The arm is involved, the photo was captured at an angle — 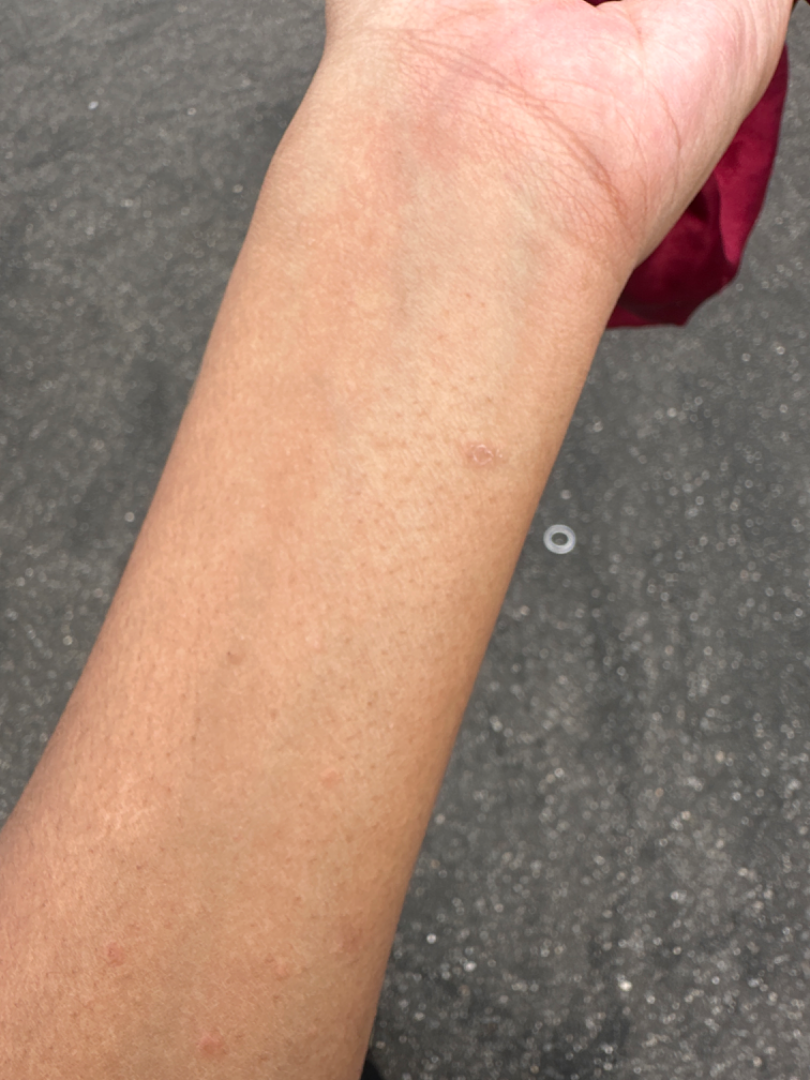{
  "systemic_symptoms": "none reported",
  "duration": "one to four weeks",
  "skin_tone": {
    "fitzpatrick": "II",
    "monk_skin_tone": [
      4,
      5
    ]
  },
  "differential": {
    "leading": [
      "Pityriasis rosea"
    ],
    "considered": [
      "Small plaque parapsoriasis"
    ],
    "unlikely": [
      "Syphilis"
    ]
  }
}